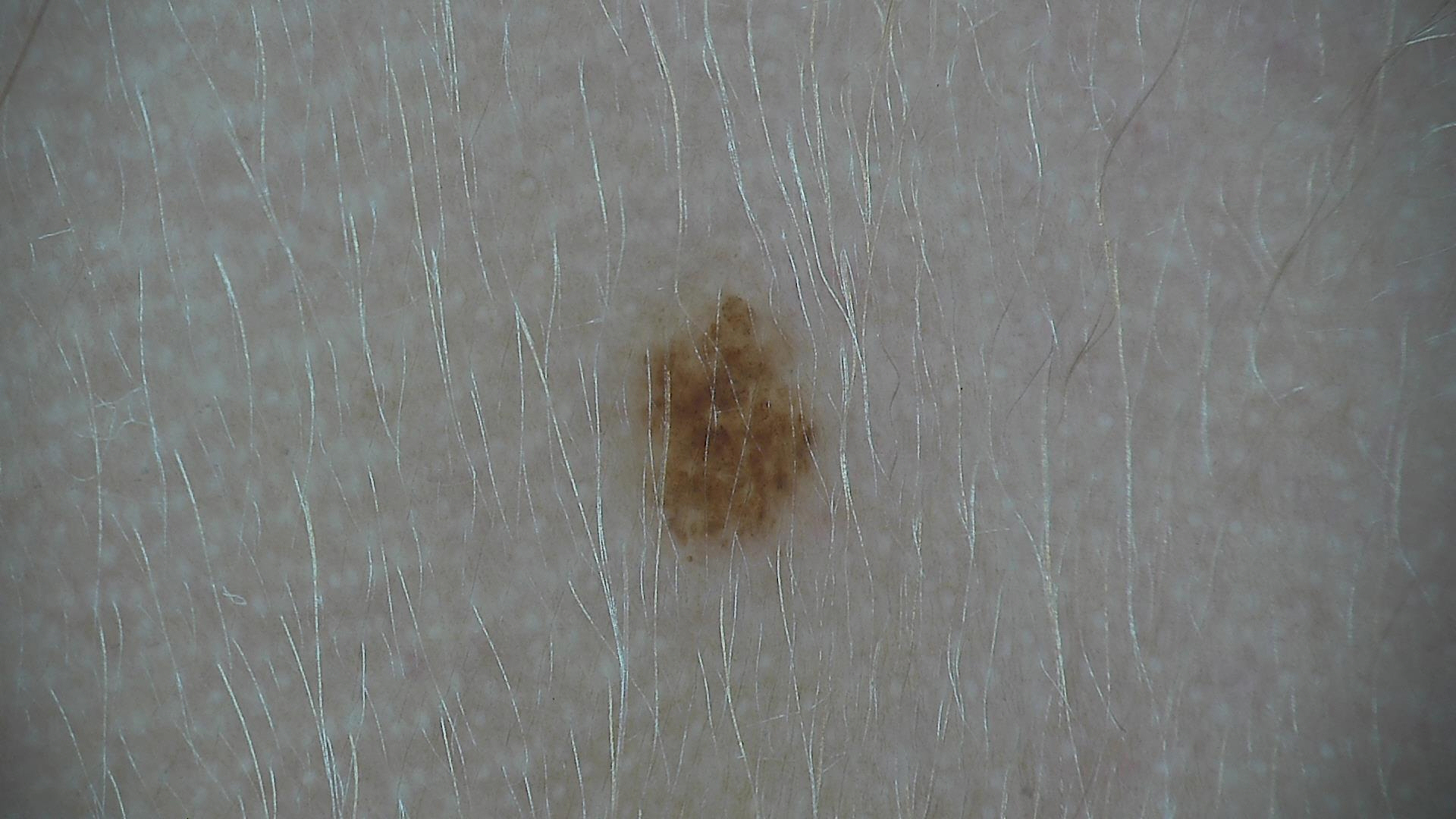Findings:
* imaging · dermatoscopy
* lesion type · banal
* diagnostic label · junctional nevus (expert consensus)